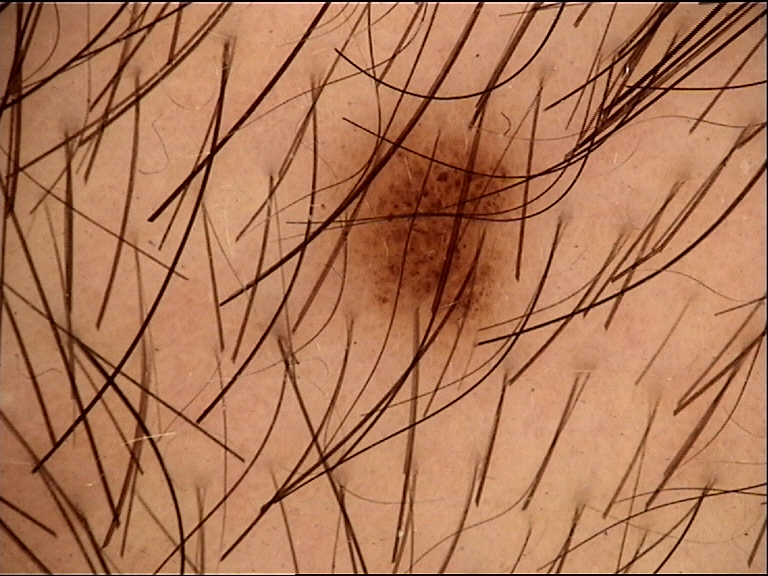A dermoscopic close-up of a skin lesion.
Consistent with a banal lesion — a junctional nevus.